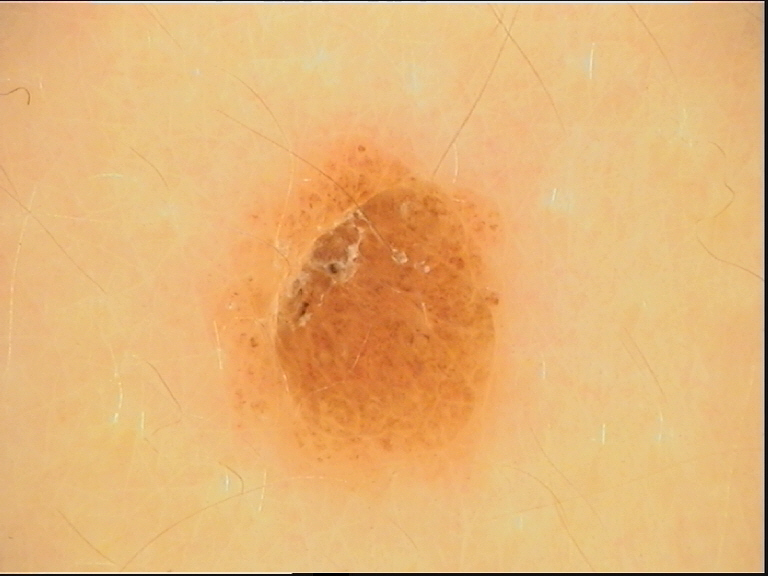The diagnostic label was a compound nevus.